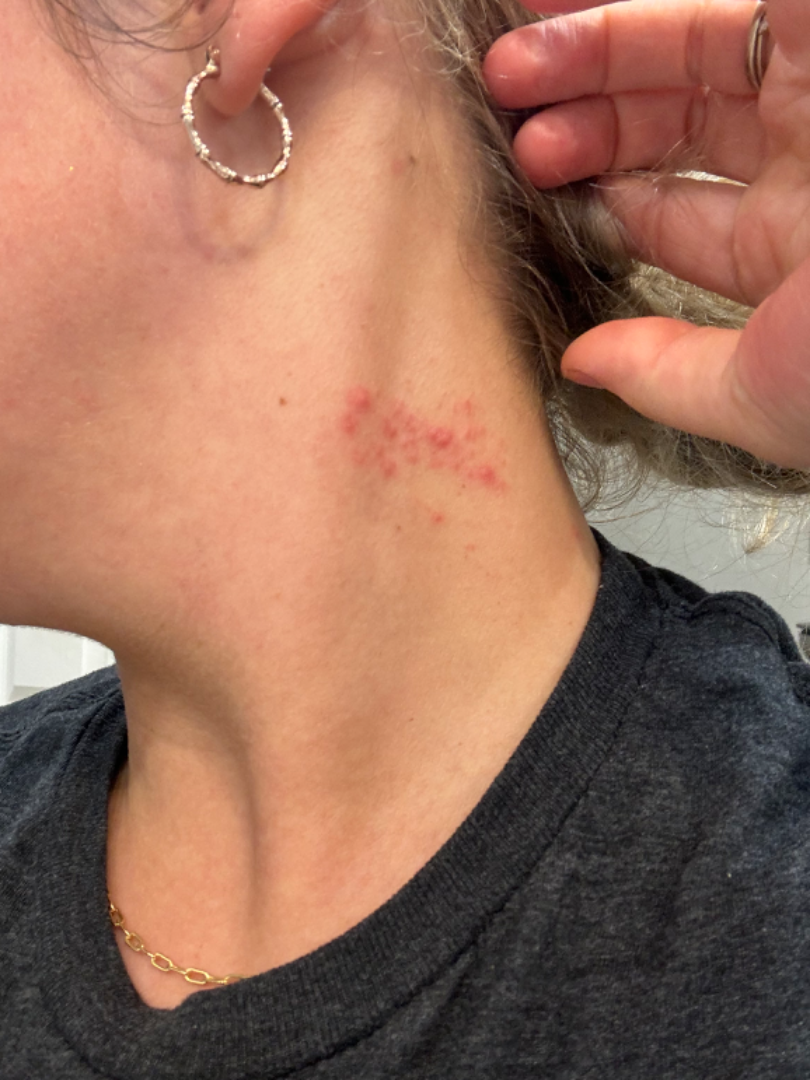<report>
  <differential>Herpes Zoster, Allergic Contact Dermatitis, Herpes Simplex</differential>
</report>